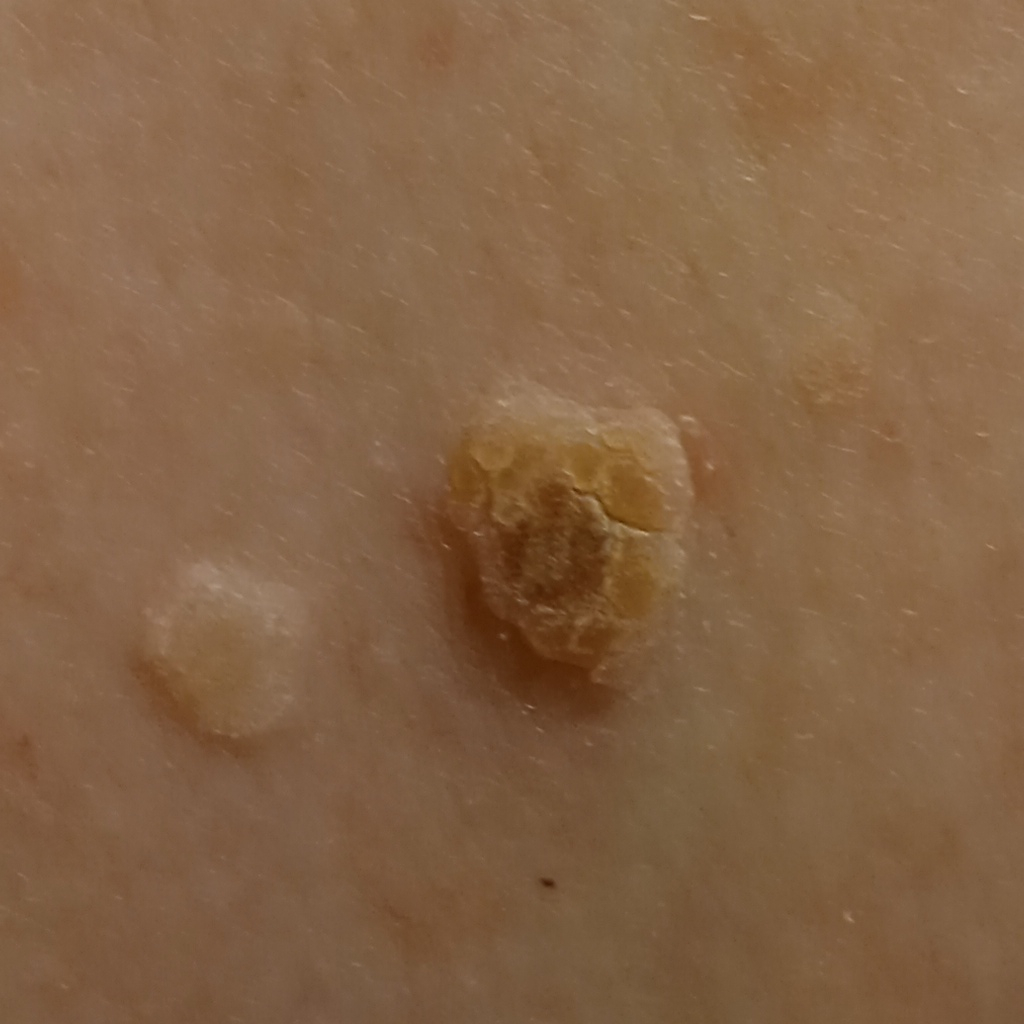The lesion was assessed as an actinic keratosis.